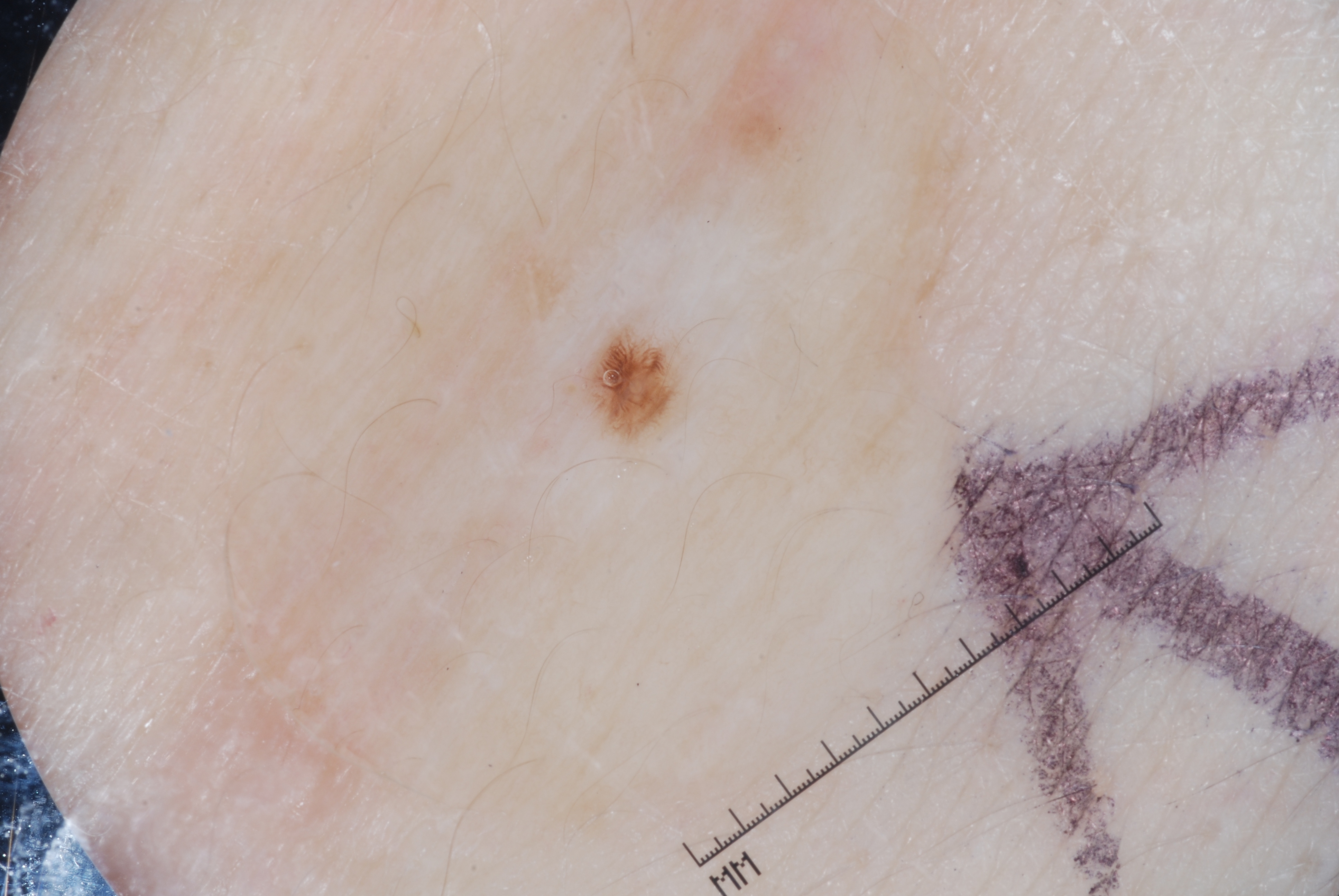Image and clinical context:
A dermatoscopic image of a skin lesion. The patient is a female in their mid- to late 40s. With coordinates (x1, y1, x2, y2), the lesion is located at [578, 322, 688, 446]. Dermoscopically, the lesion shows pigment network. The lesion occupies roughly 1% of the field.
Conclusion:
The lesion was assessed as a melanocytic nevus, a benign lesion.